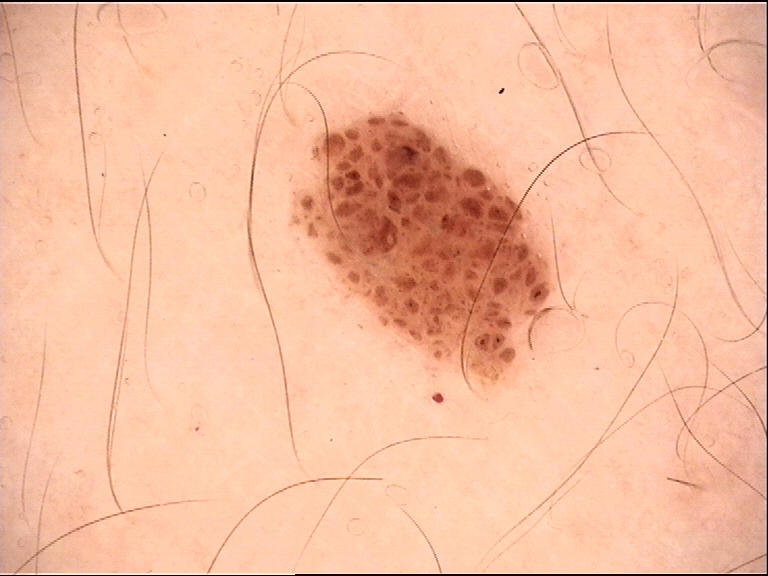Q: How is the lesion classified?
A: banal
Q: What is the diagnosis?
A: compound nevus (expert consensus)